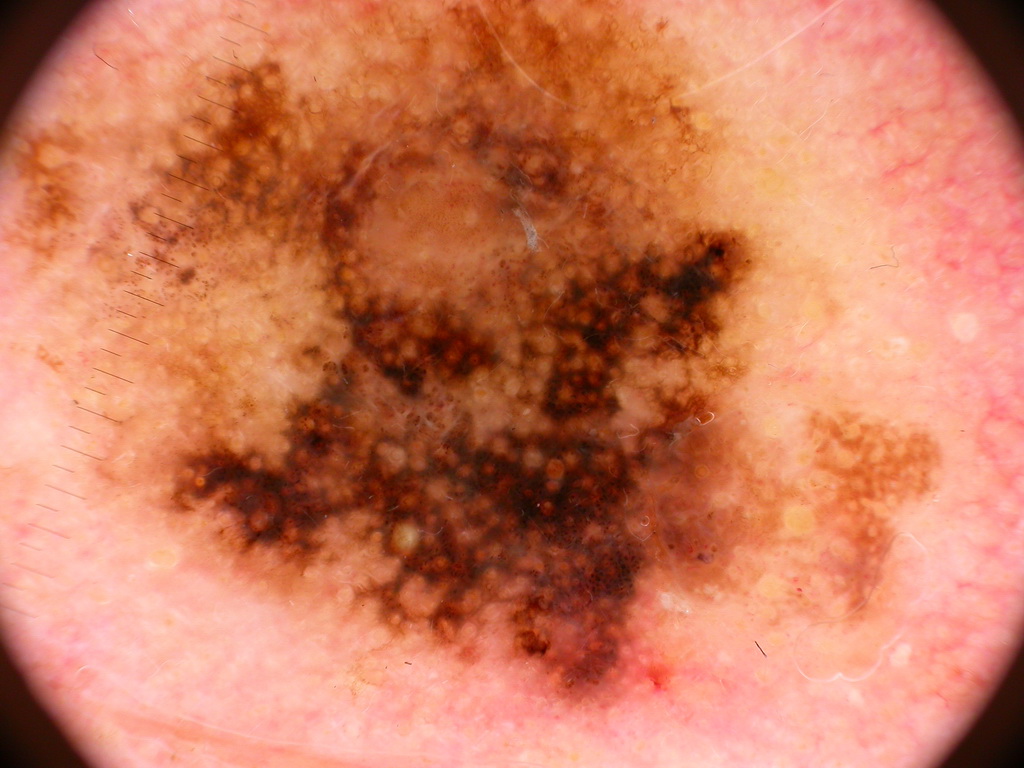modality = dermoscopic image
dermoscopic pattern = globules; absent: pigment network, streaks, milia-like cysts, and negative network
field coverage = reaches across the whole image
diagnostic label = a melanoma